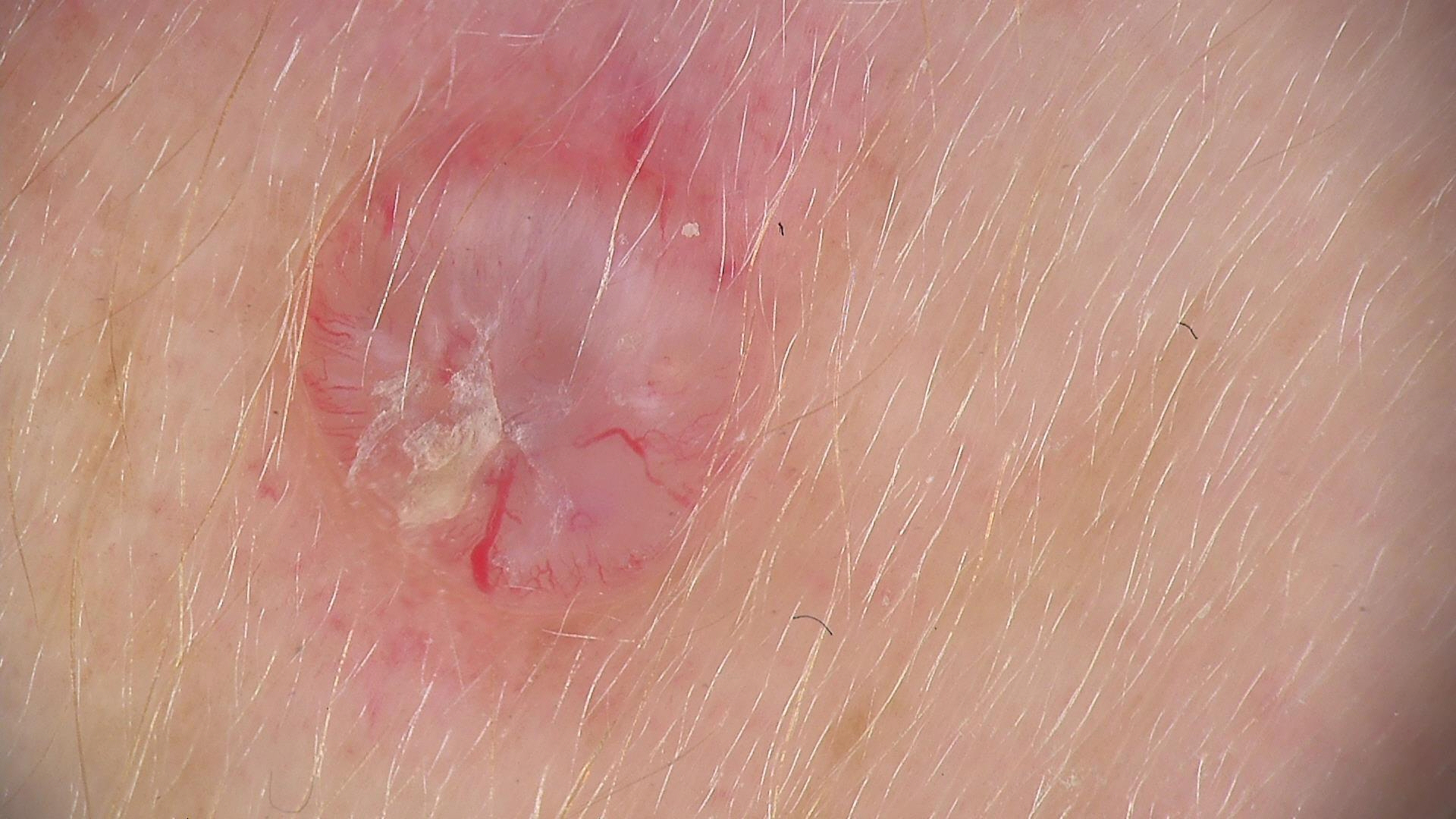Case:
* pathology — basal cell carcinoma (biopsy-proven)